A skin lesion imaged with a dermatoscope.
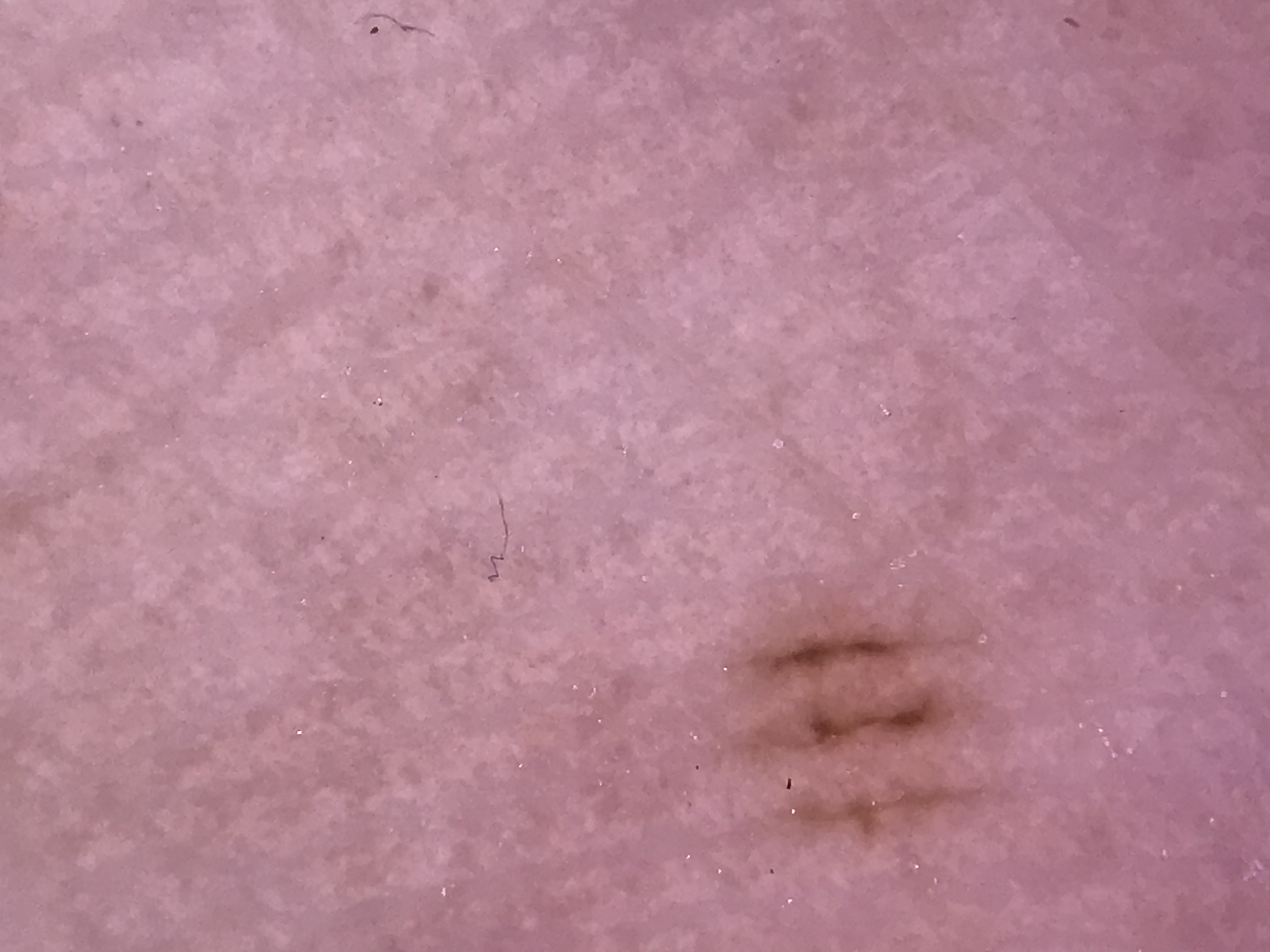The architecture is that of a banal lesion.
Consistent with an acral junctional nevus.